A male subject aged approximately 65; a contact-polarized dermoscopy image of a skin lesion:
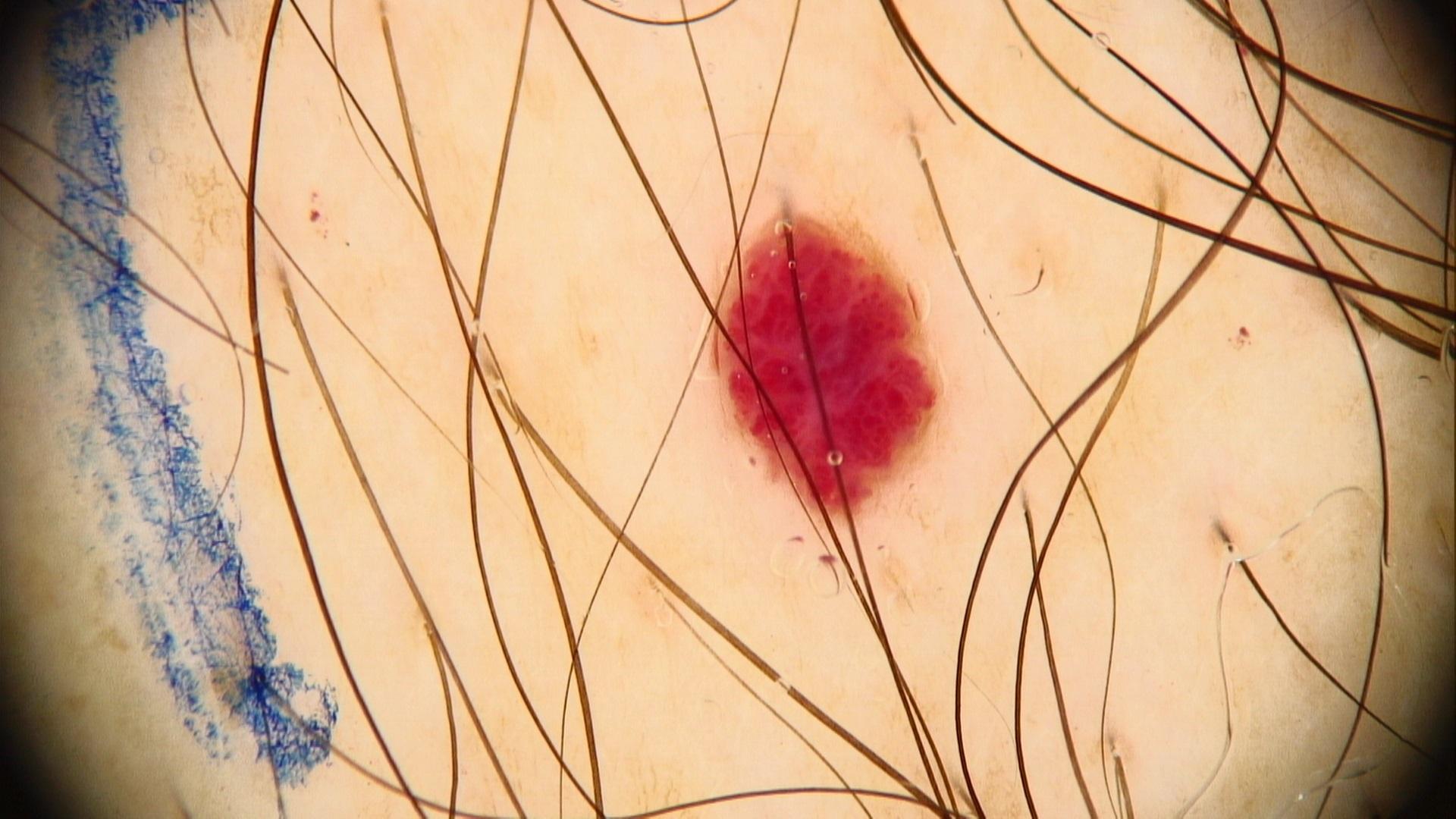Clinical context:
Located on the trunk.
Conclusion:
The clinical assessment was a vascular lesion.